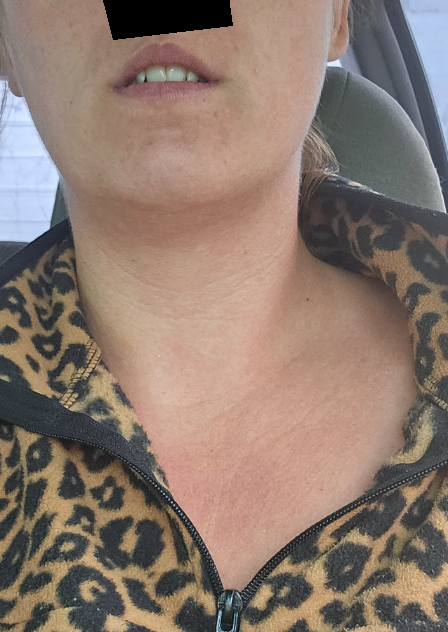The case was indeterminate on photographic review. Reported lesion symptoms include itching and bothersome appearance. Fitzpatrick phototype III; lay graders estimated 2 on the Monk skin tone scale. An image taken at a distance. The head or neck is involved.